The arm is involved. The subject is male. An image taken at an angle.
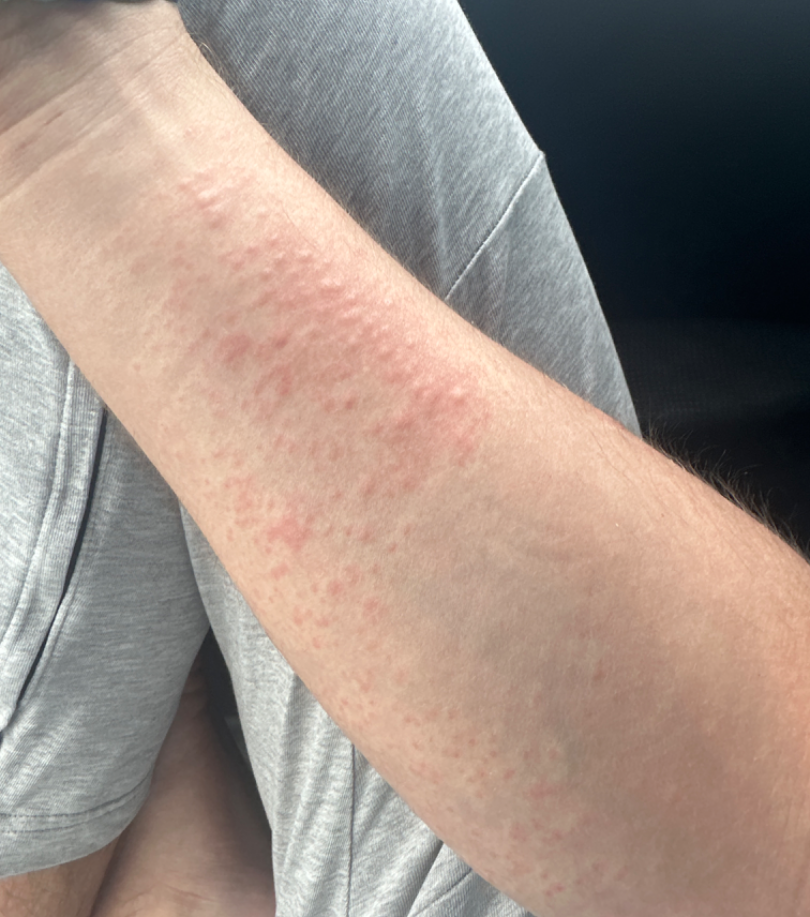differential diagnosis — reviewed remotely by three dermatologists: most consistent with Urticaria; also consider Allergic Contact Dermatitis; less likely is Eczema.